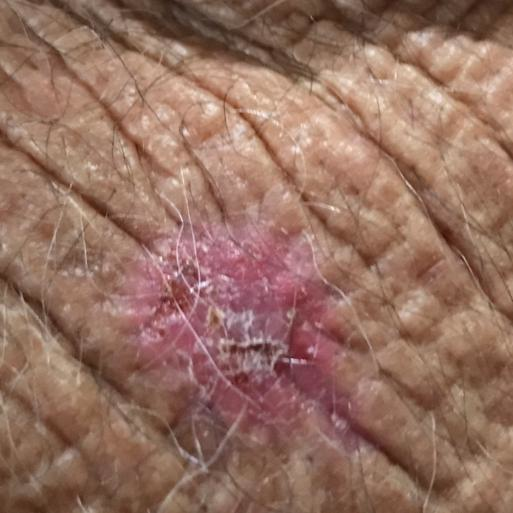Q: What is the patient's skin type?
A: II
Q: What is the imaging modality?
A: smartphone clinical photo
Q: Any relevant history?
A: pesticide exposure, prior malignancy (patient or family), prior skin cancer (patient or family), no tobacco use
Q: Patient demographics?
A: male, in their 70s
Q: Where on the body is the lesion?
A: a forearm
Q: Lesion size?
A: 15x10 mm
Q: What symptoms does the patient report?
A: pain, itching, elevation, bleeding / no growth
Q: What is this lesion?
A: basal cell carcinoma (biopsy-proven)